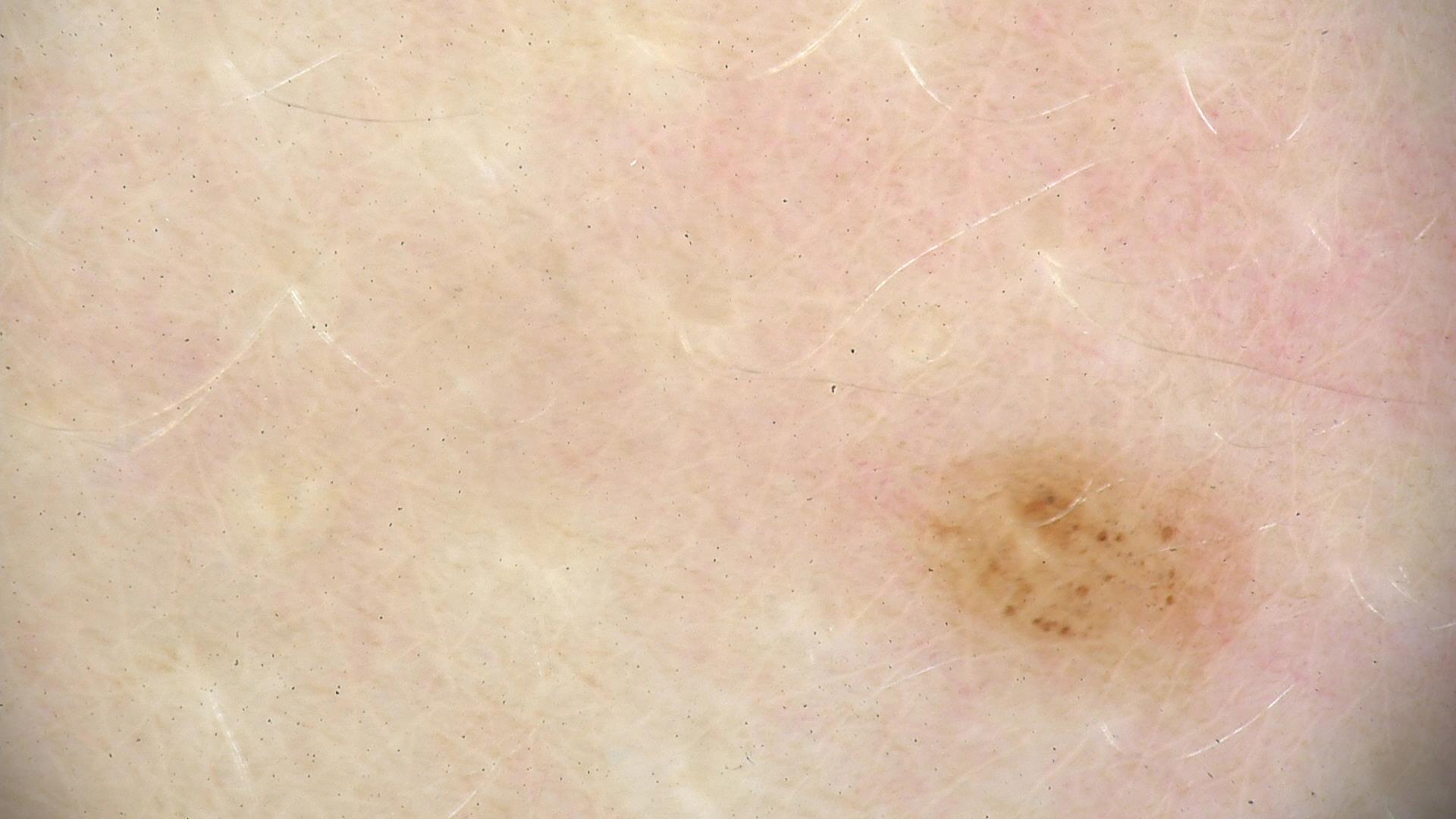diagnostic label = dysplastic junctional nevus (expert consensus).